A patient in their 30s · a clinical photograph showing a skin lesion: 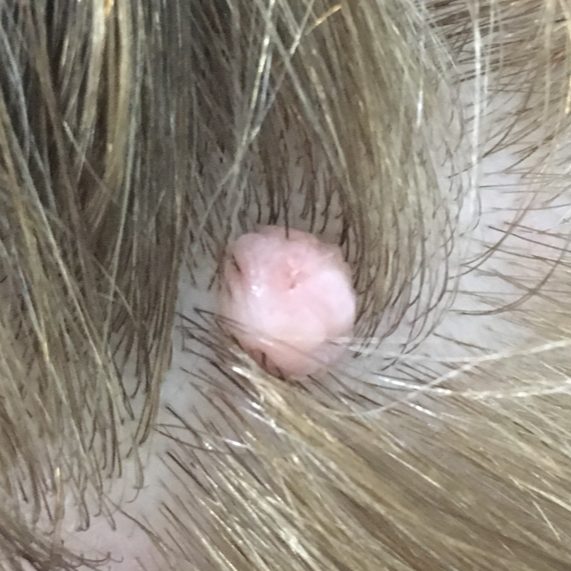Notes:
- anatomic site · the scalp
- diagnostic label · nevus (clinical consensus)